The lesion is associated with bothersome appearance, enlargement, pain, itching and burning; the condition has been present for less than one week; the photo was captured at a distance; the contributor reports the lesion is raised or bumpy and rough or flaky: 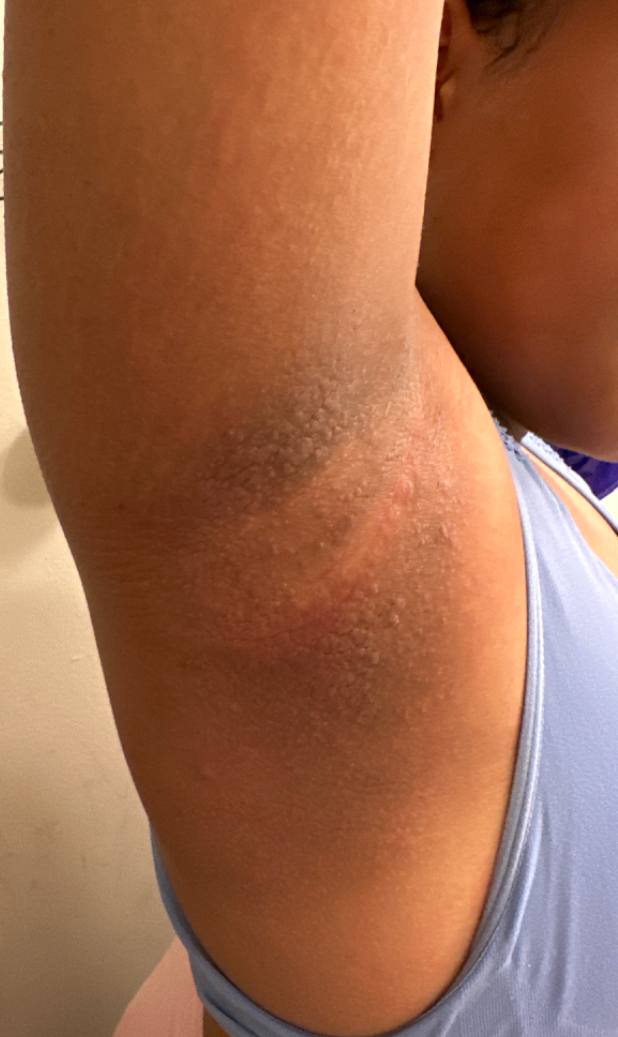{
  "differential": {
    "leading": [
      "Acanthosis nigricans"
    ]
  }
}